No associated systemic symptoms reported · the leg, head or neck and arm are involved · the subject is 18–29, male · the lesion is associated with pain, enlargement and itching · reported duration is less than one week · the photo was captured at an angle · the patient described the issue as a rash · the lesion is described as raised or bumpy:
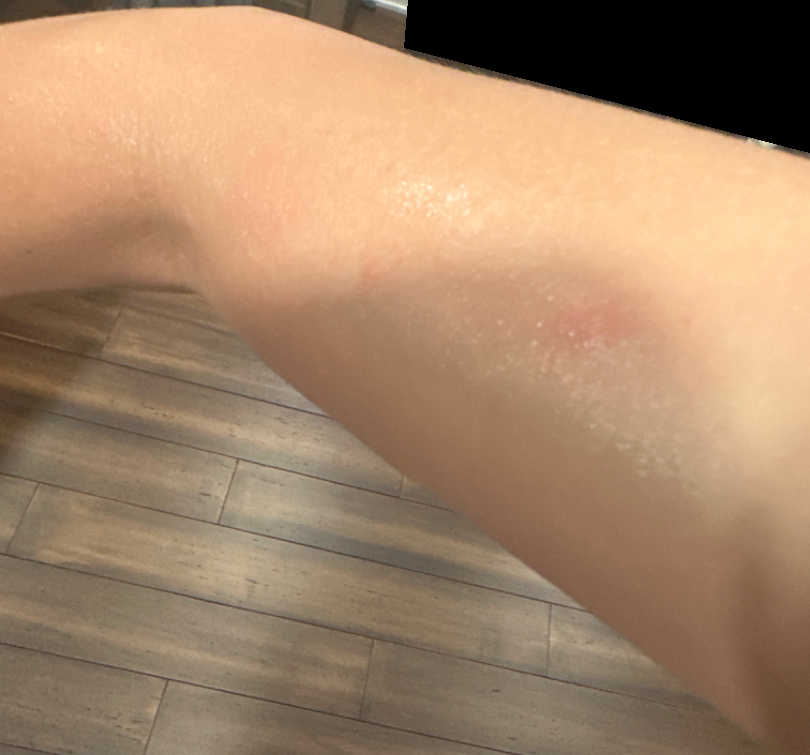Most likely Urticaria; possibly Acute dermatitis, NOS; lower on the differential is Allergic Contact Dermatitis; less probable is Eczema.